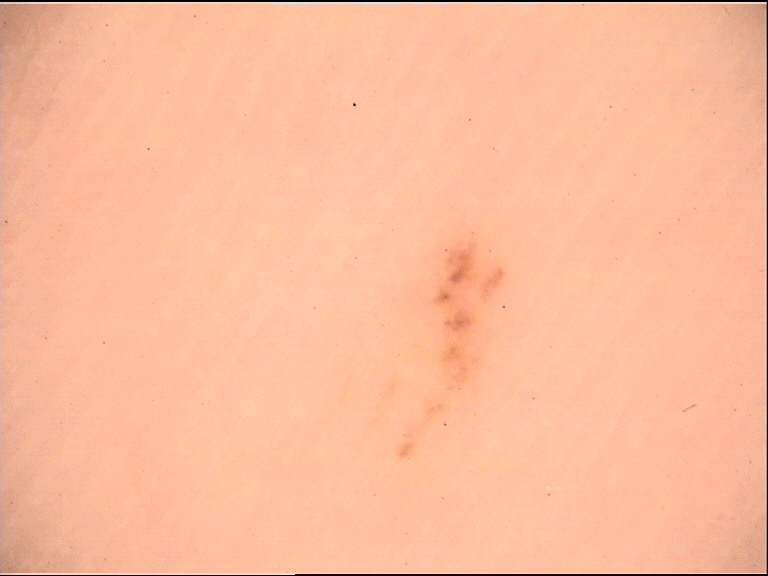The morphology is that of a banal lesion. The diagnostic label was an acral junctional nevus.